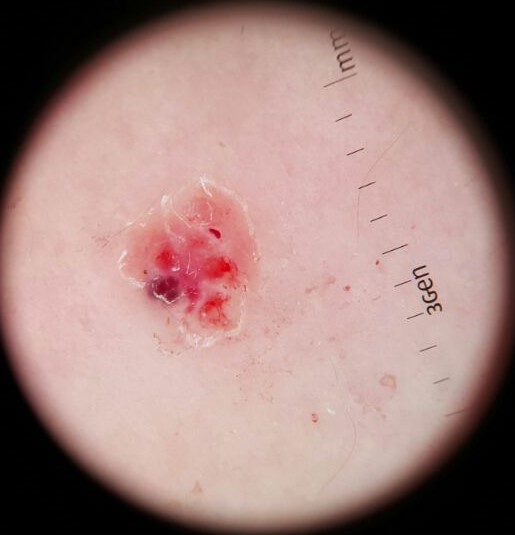Findings: The architecture is that of a vascular lesion. Impression: Diagnosed as a benign lesion — an angiokeratoma.